A dermatoscopic image of a skin lesion; a male subject, about 45 years old — 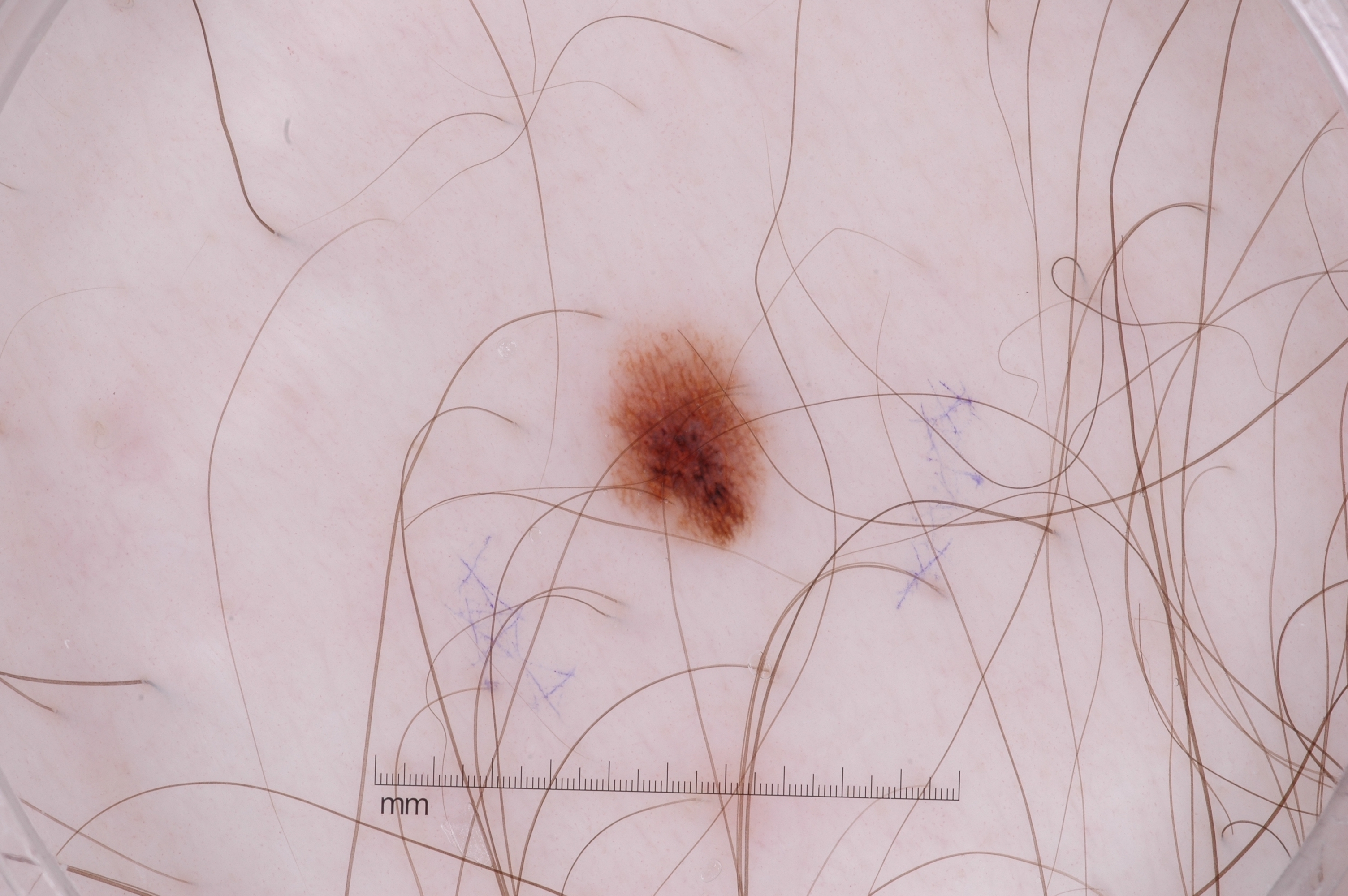Findings:
Dermoscopy demonstrates pigment network. The lesion covers approximately 2% of the dermoscopic field. In (x1, y1, x2, y2) order, the lesion's extent is [601,329,769,539].
Conclusion:
Diagnosed as a melanocytic nevus.